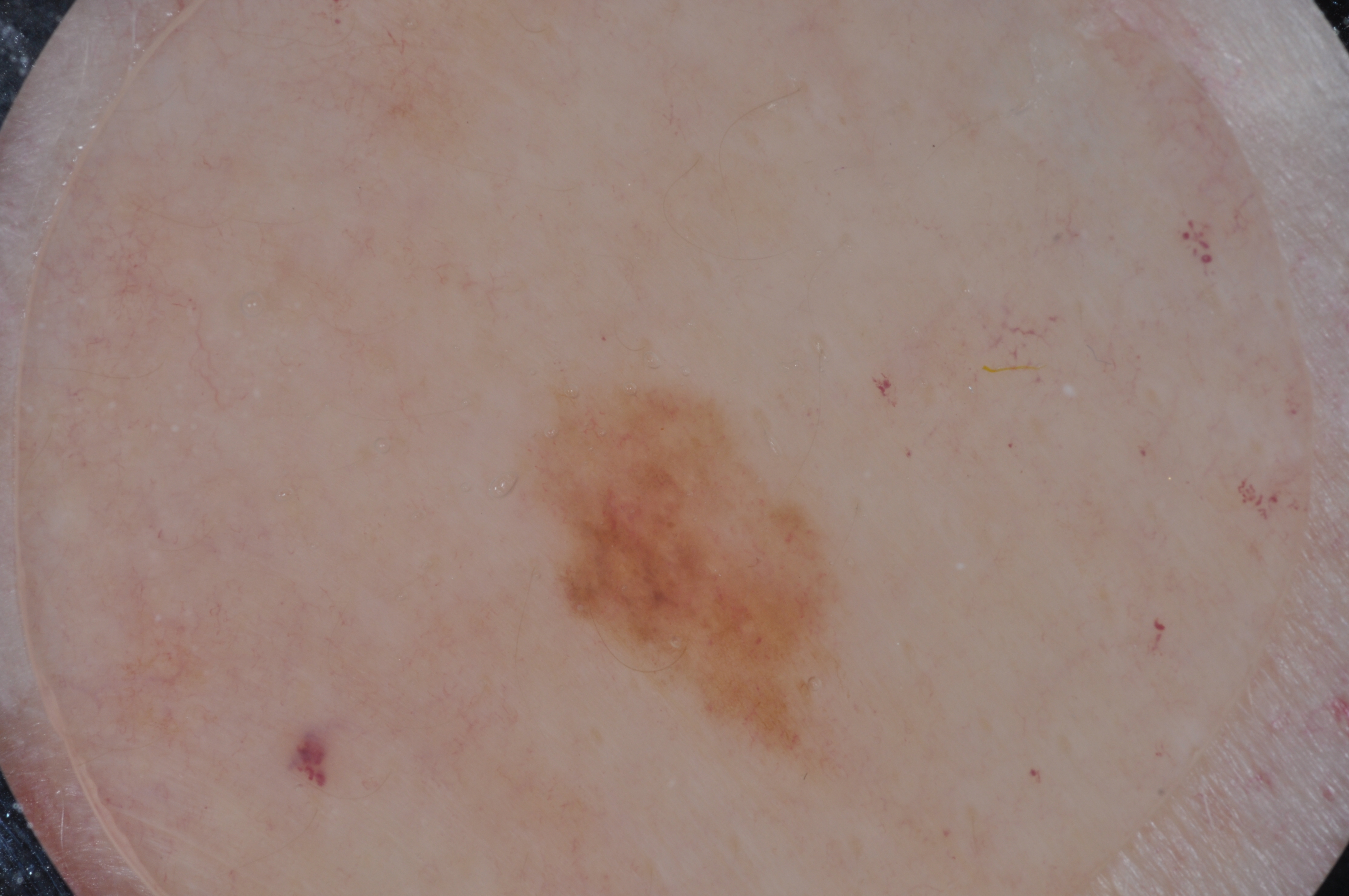image — dermoscopy of a skin lesion
patient — female, about 80 years old
dermoscopic pattern — pigment network; absent: negative network, streaks, and milia-like cysts
size — small
location — 538 385 832 735
assessment — a melanoma, a skin cancer